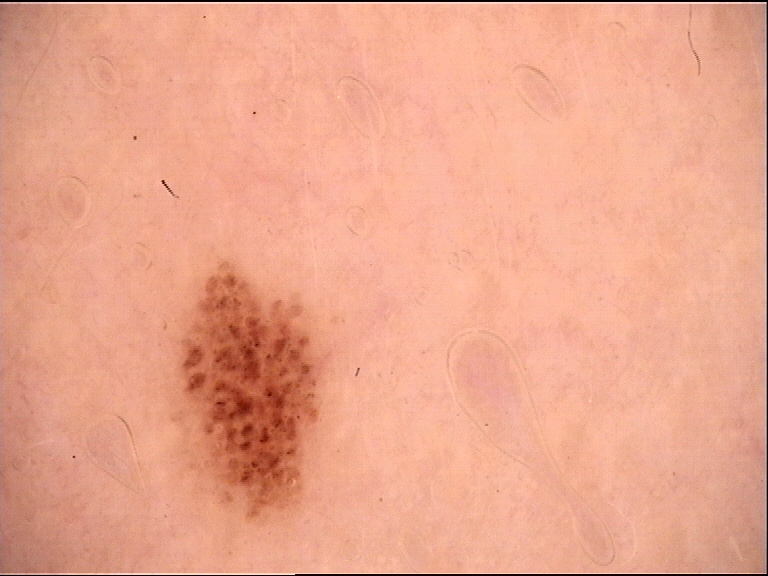{
  "lesion_type": {
    "main_class": "banal",
    "pattern": "junctional"
  },
  "diagnosis": {
    "name": "junctional nevus",
    "code": "jb",
    "malignancy": "benign",
    "super_class": "melanocytic",
    "confirmation": "expert consensus"
  }
}